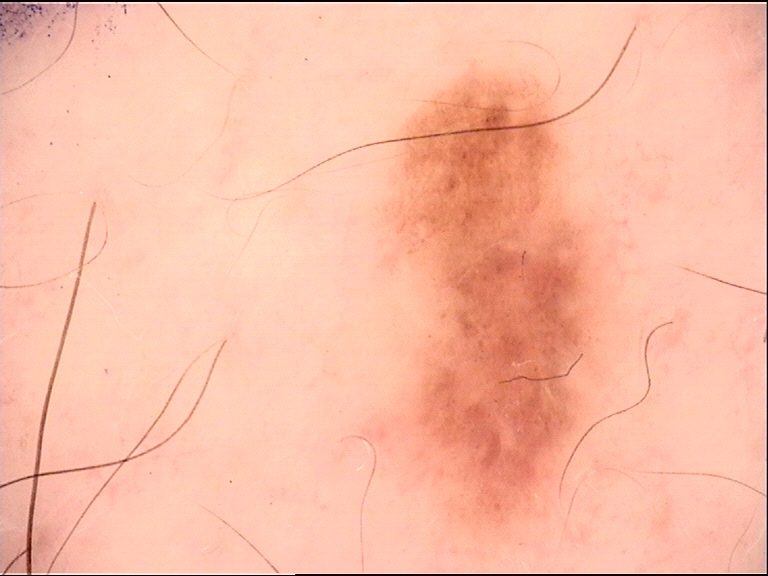image: dermatoscopy
diagnosis:
  name: dysplastic junctional nevus
  code: jd
  malignancy: benign
  super_class: melanocytic
  confirmation: expert consensus